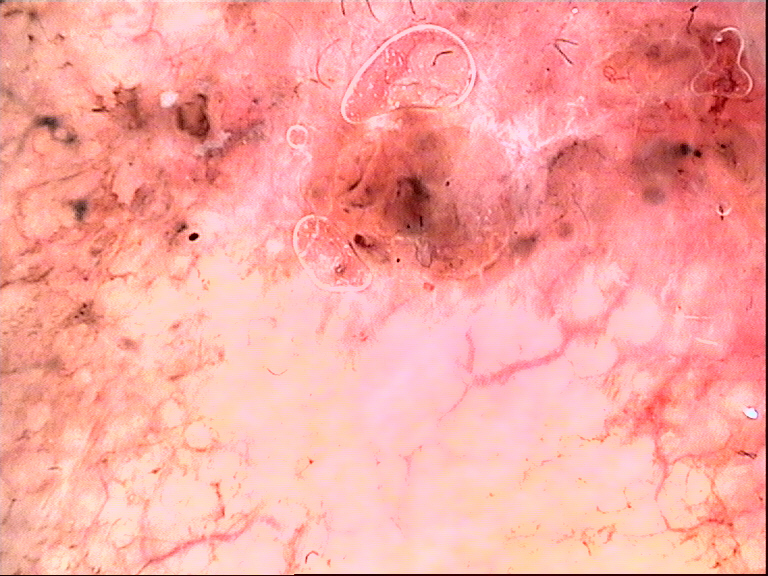A dermoscopic close-up of a skin lesion. The biopsy diagnosis was a keratinocytic lesion — a basal cell carcinoma.